A dermoscopic view of a skin lesion — 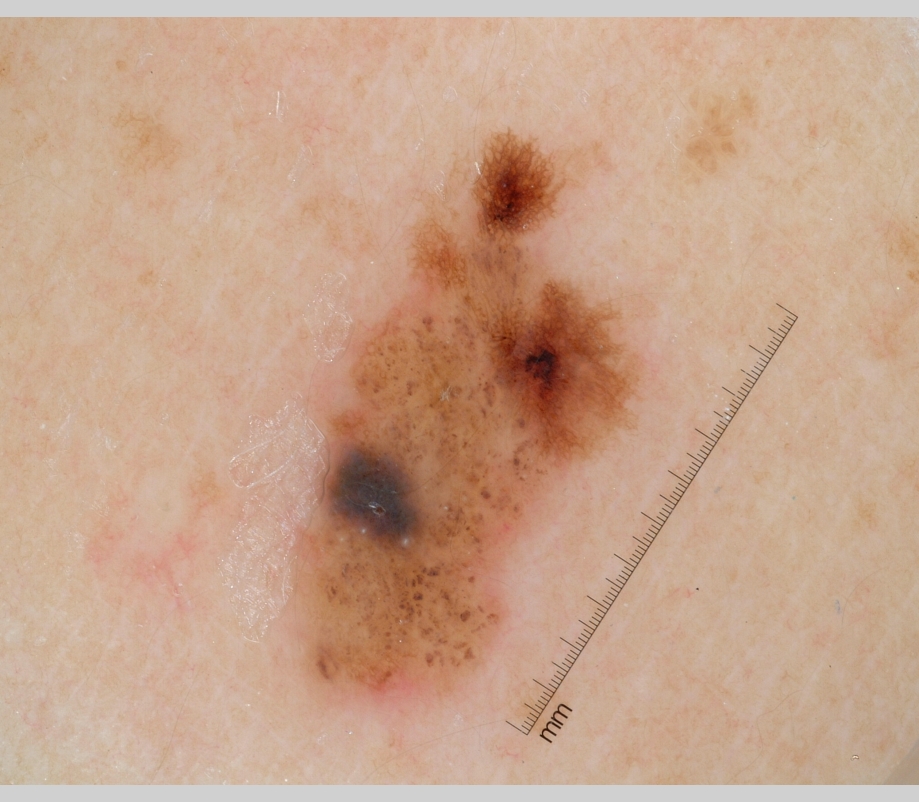As (left, top, right, bottom), the lesion spans bbox=[293, 131, 639, 698].
The lesion covers approximately 15% of the dermoscopic field.
Dermoscopy demonstrates globules and pigment network; no milia-like cysts, negative network, or streaks.
Consistent with a melanocytic nevus, a benign skin lesion.